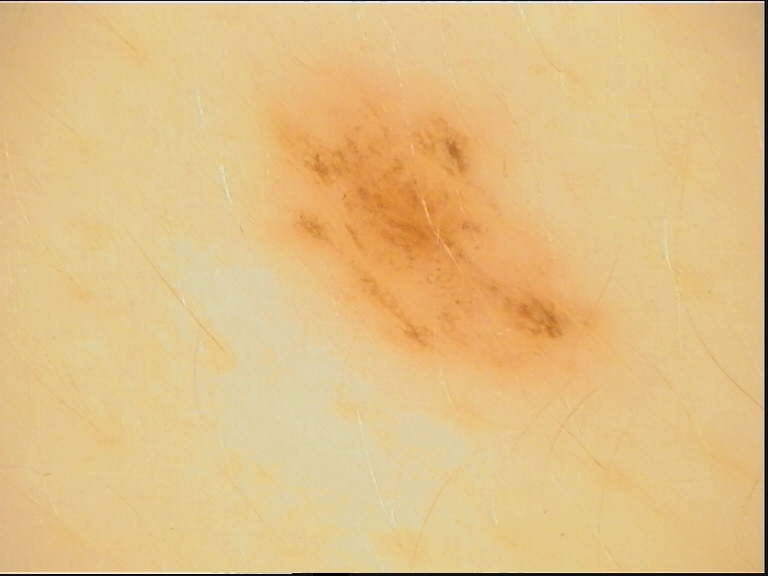Q: What is this lesion?
A: dysplastic junctional nevus (expert consensus)